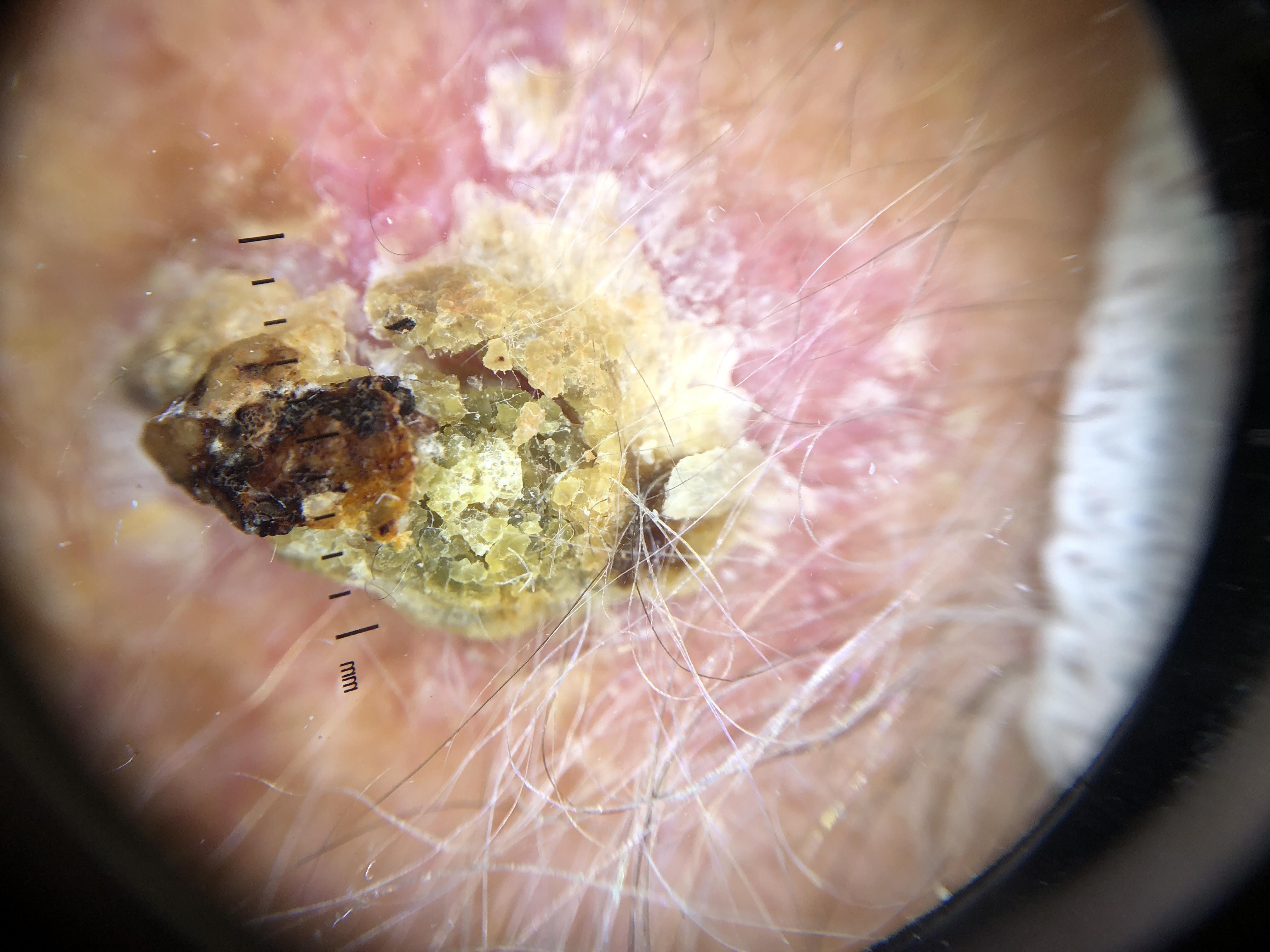{
  "patient": {
    "age_approx": "85+",
    "sex": "female"
  },
  "image": "contact-polarized dermoscopy",
  "skin_type": "II",
  "lesion_location": {
    "region": "the head or neck"
  },
  "diagnosis": {
    "name": "Squamous cell carcinoma",
    "malignancy": "malignant",
    "confirmation": "histopathology",
    "lineage": "epidermal"
  }
}